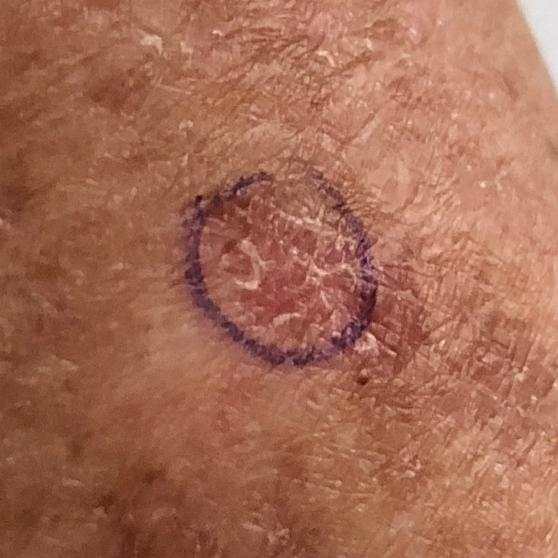The lesion involves an arm.
The consensus clinical diagnosis was an actinic keratosis.